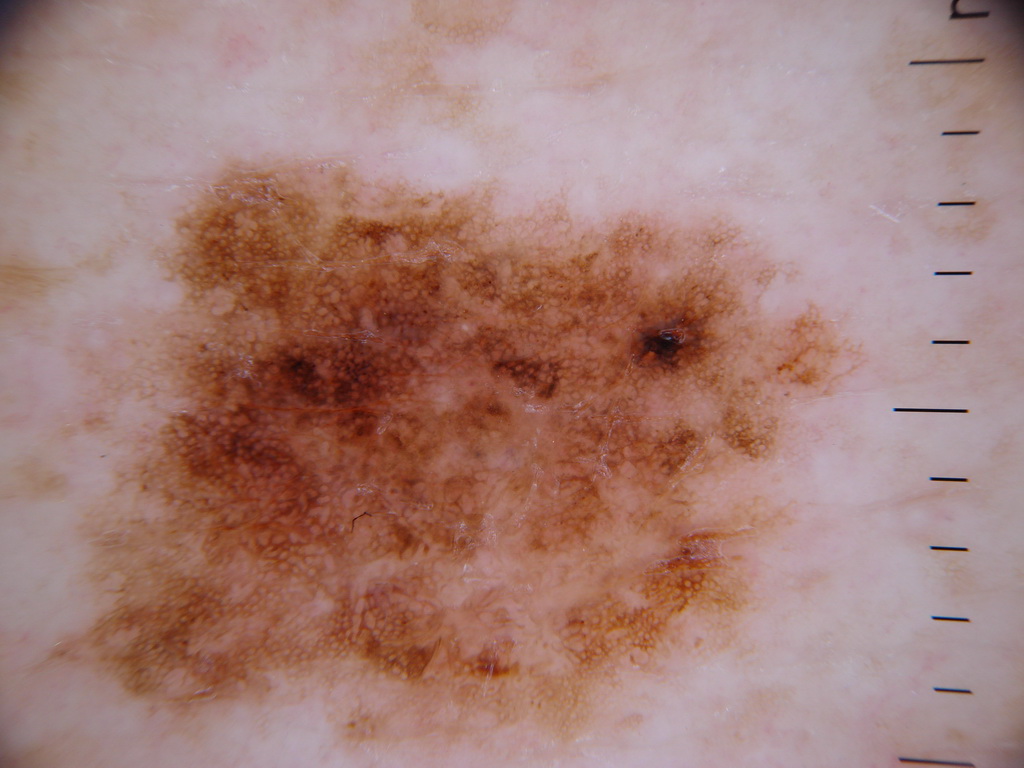modality: dermatoscopic image of a skin lesion | dermoscopic features: pigment network | lesion extent: large | location: x1=34, y1=149, x2=893, y2=765 | diagnostic label: a melanocytic nevus.